A dermoscopy image of a single skin lesion.
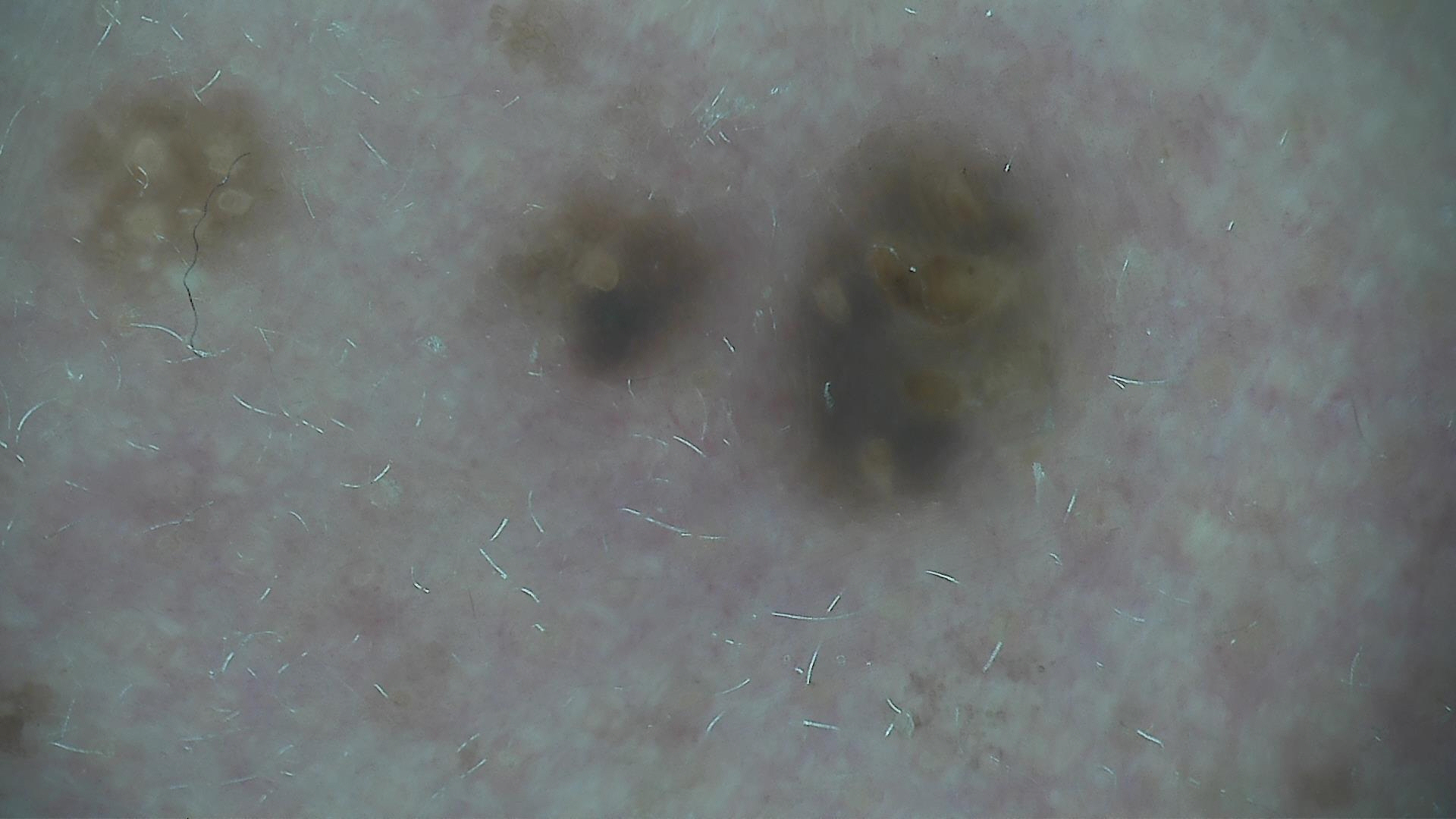subtype = keratinocytic | diagnostic label = seborrheic keratosis (expert consensus).